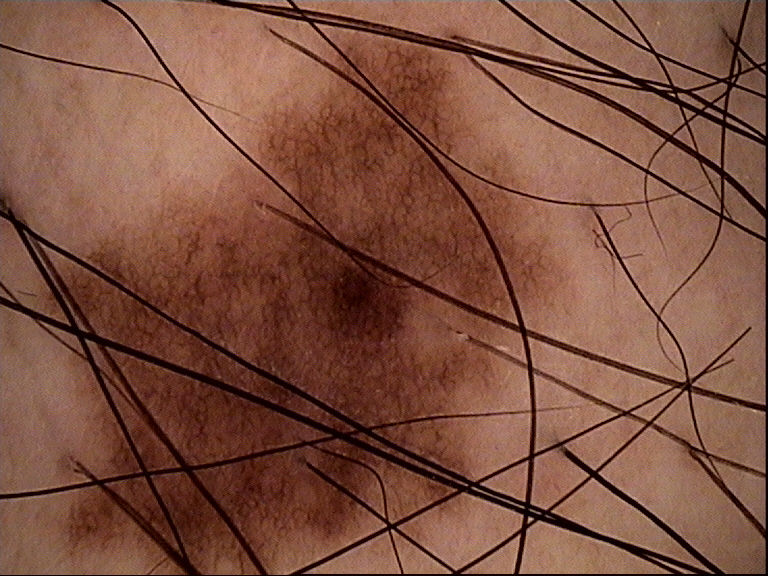Conclusion: The diagnosis was a dysplastic junctional nevus.